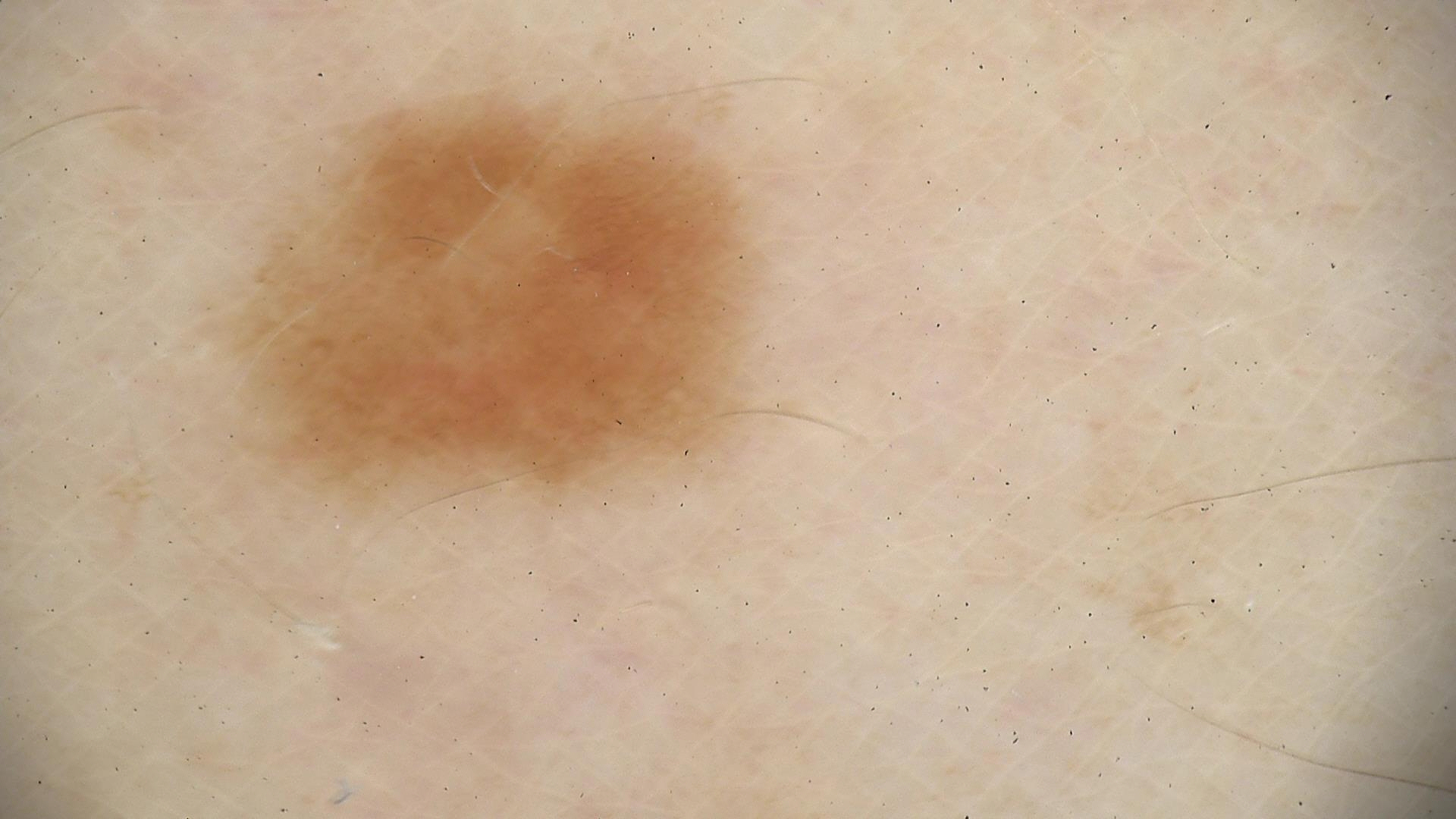assessment: dysplastic junctional nevus (expert consensus).